The patient notes the lesion is flat; reported duration is one to four weeks; the patient described the issue as a rash; the lesion is associated with enlargement, bothersome appearance and itching; the subject is 18–29, male; the back of the torso is involved; the photograph was taken at a distance:
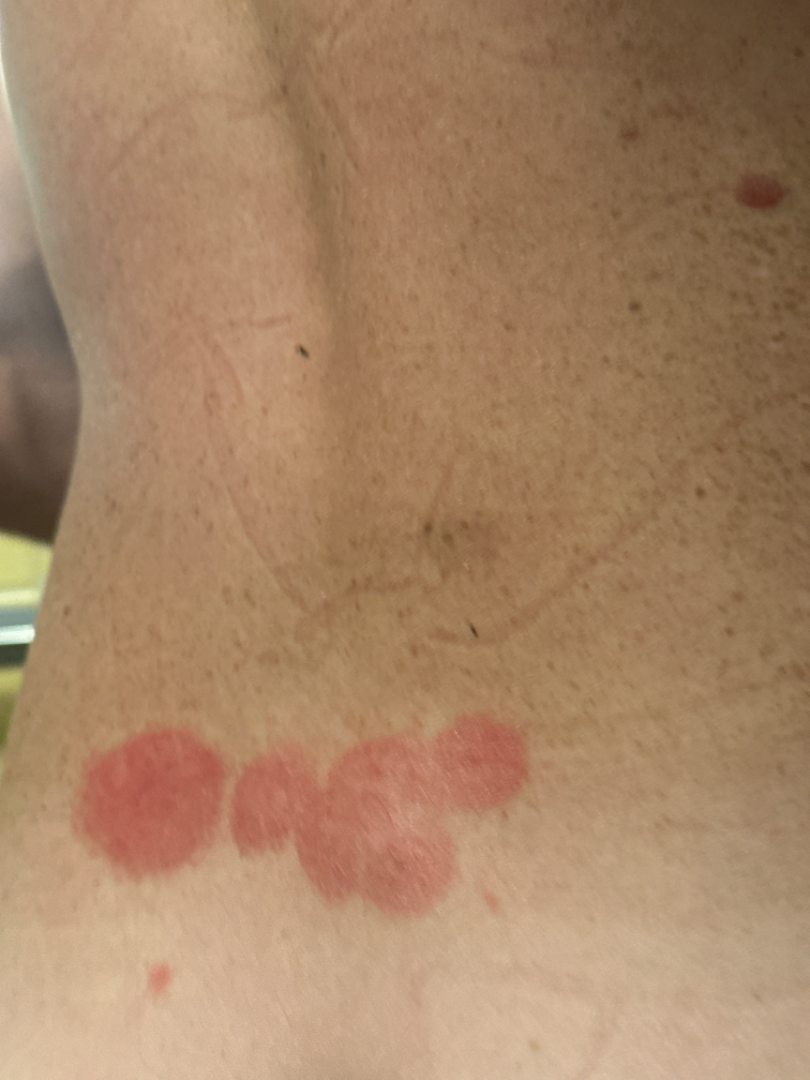| field | value |
|---|---|
| assessment | ungradable on photographic review |